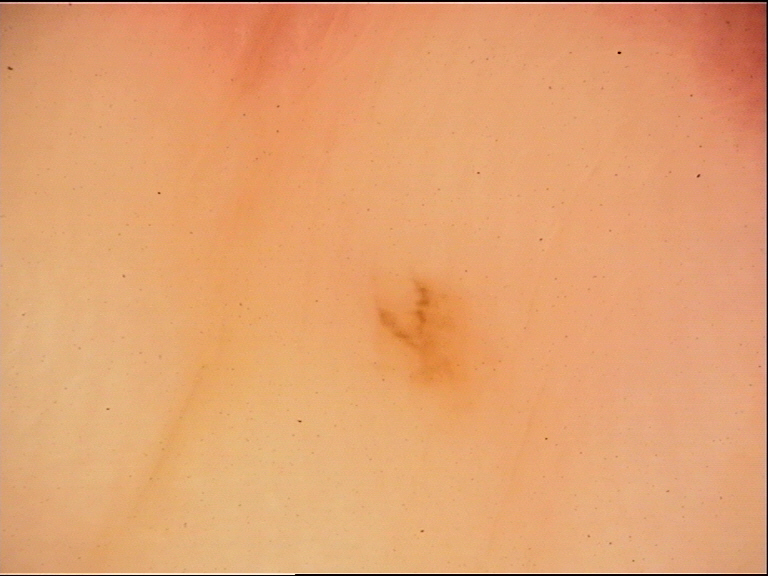<lesion>
  <diagnosis>
    <name>acral junctional nevus</name>
    <code>ajb</code>
    <malignancy>benign</malignancy>
    <super_class>melanocytic</super_class>
    <confirmation>expert consensus</confirmation>
  </diagnosis>
</lesion>